A male patient, approximately 80 years of age. A dermatoscopic image of a skin lesion — 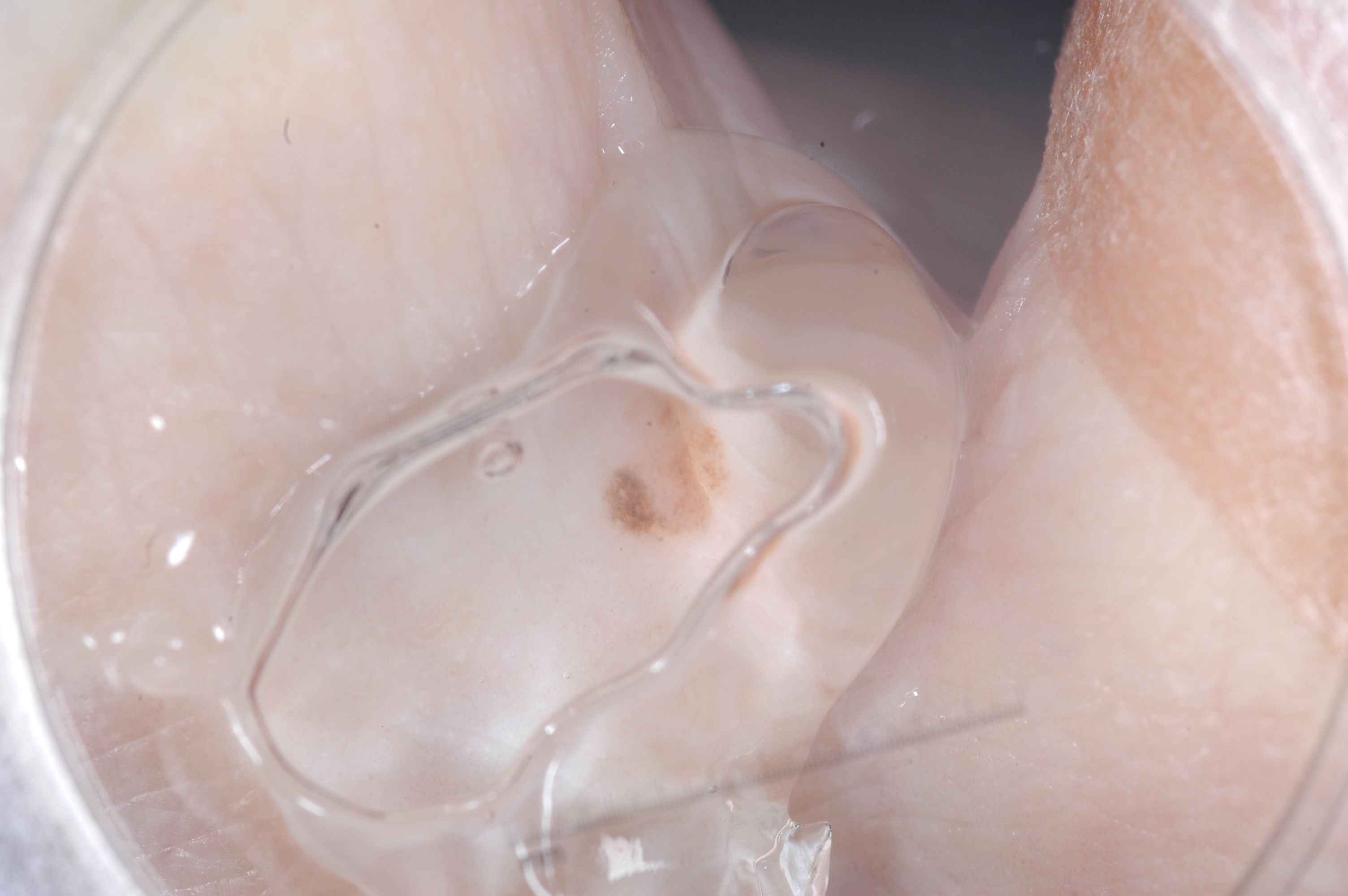The visible lesion spans bbox(599, 383, 737, 546). The dermoscopic pattern shows pigment network; no negative network, milia-like cysts, or streaks. The lesion was assessed as a melanocytic nevus, a benign lesion.